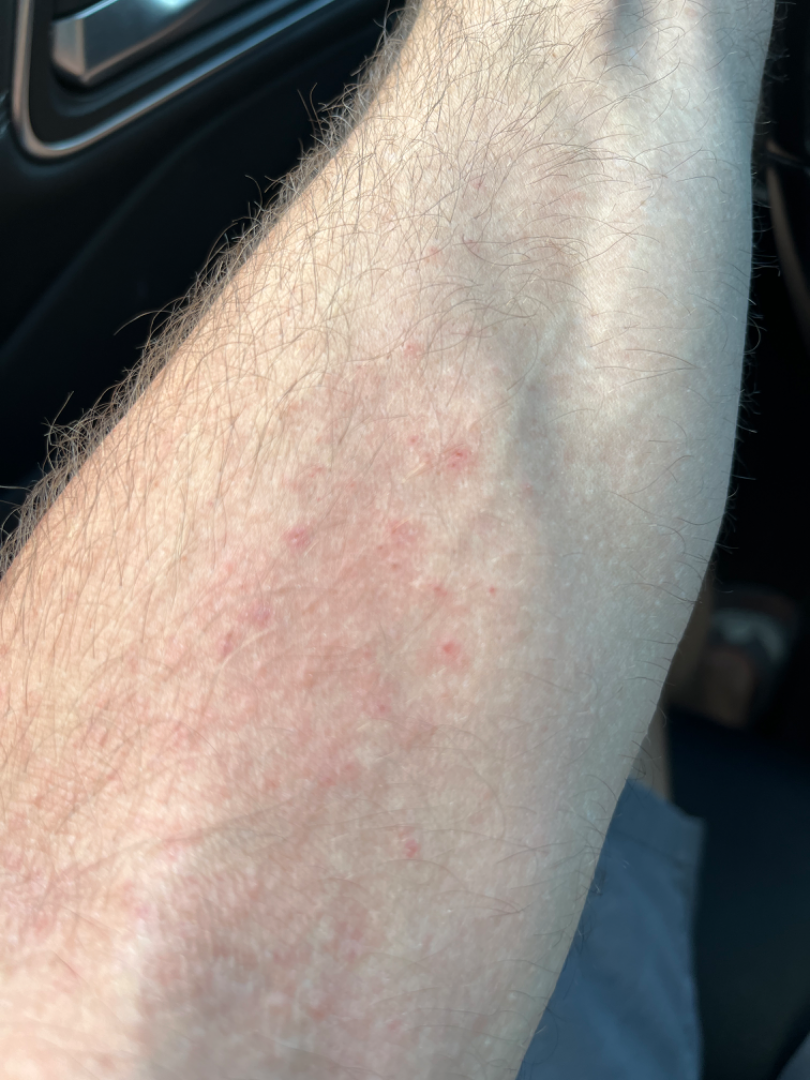impression = the leading consideration is Eczema; an alternative is Drug Rash; also raised was Allergic Contact Dermatitis